A female subject age 48. Dermoscopy of a skin lesion: 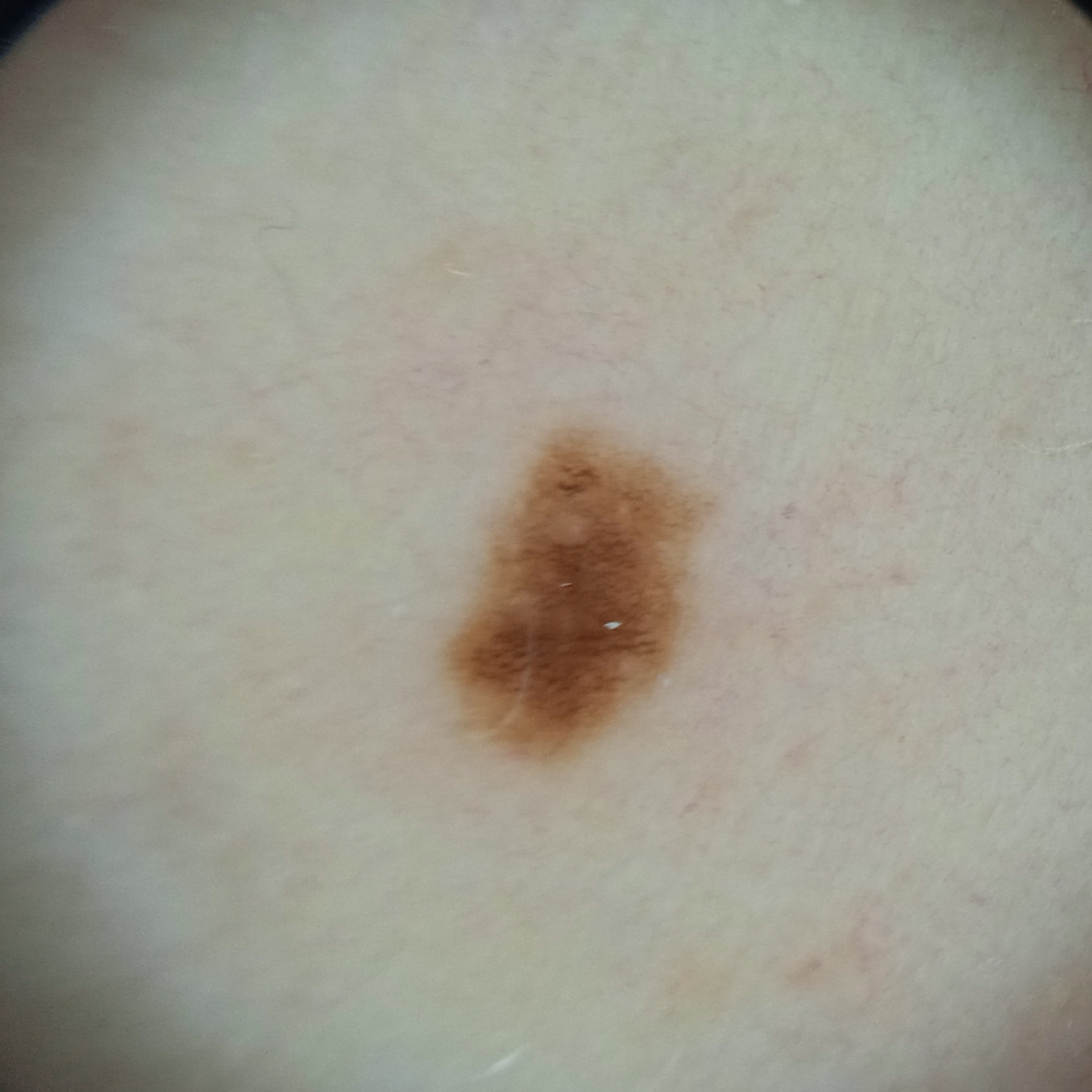  lesion_location: the torso
  lesion_size:
    diameter_mm: 4.3
  diagnosis:
    name: melanocytic nevus
    malignancy: benign